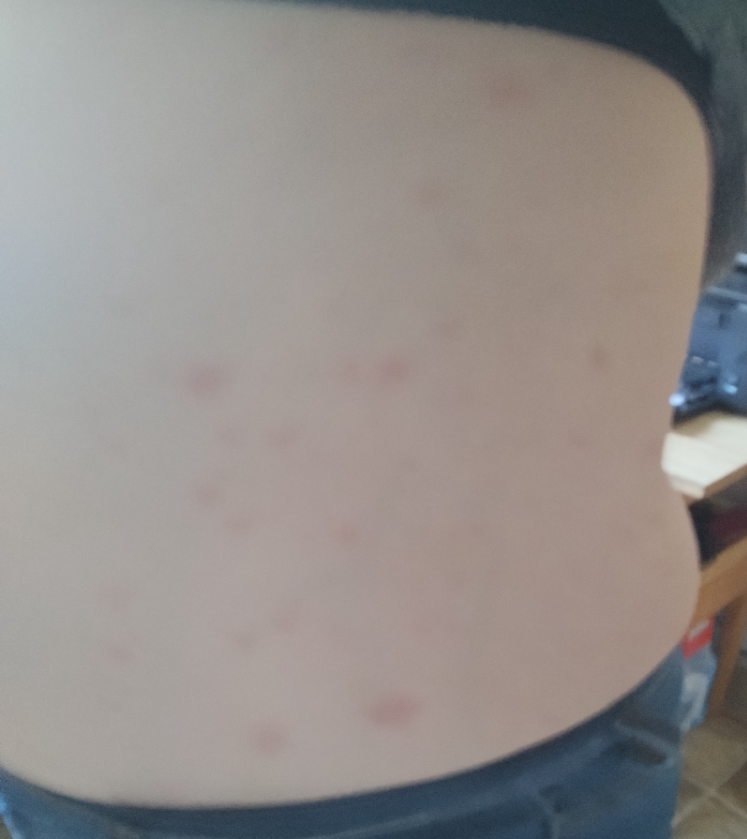| field | value |
|---|---|
| assessment | ungradable on photographic review |
| image framing | close-up |
| patient describes the issue as | a rash |
| symptoms | enlargement and bothersome appearance |
| affected area | leg, back of the torso, front of the torso, head or neck and arm |
| subject | female, age 60–69 |
| surface texture | rough or flaky and flat |